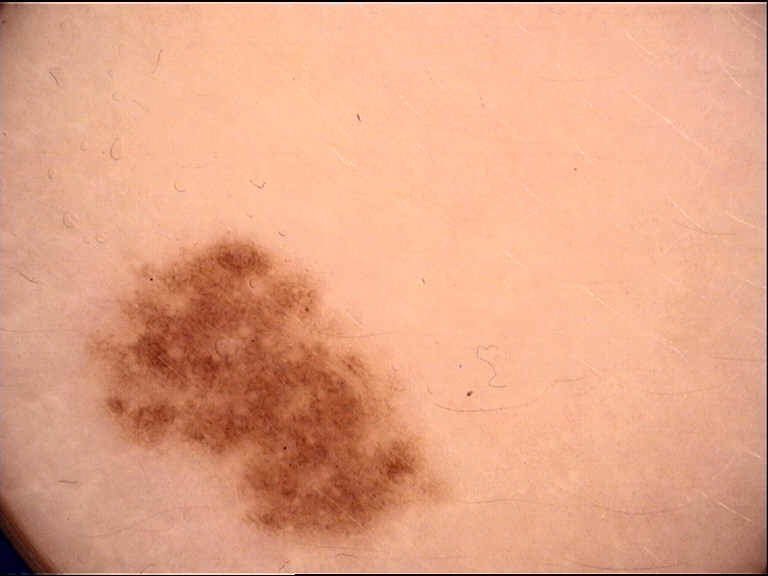assessment — congenital junctional nevus (expert consensus).